A female patient, aged around 70 · a dermoscopic view of a skin lesion — 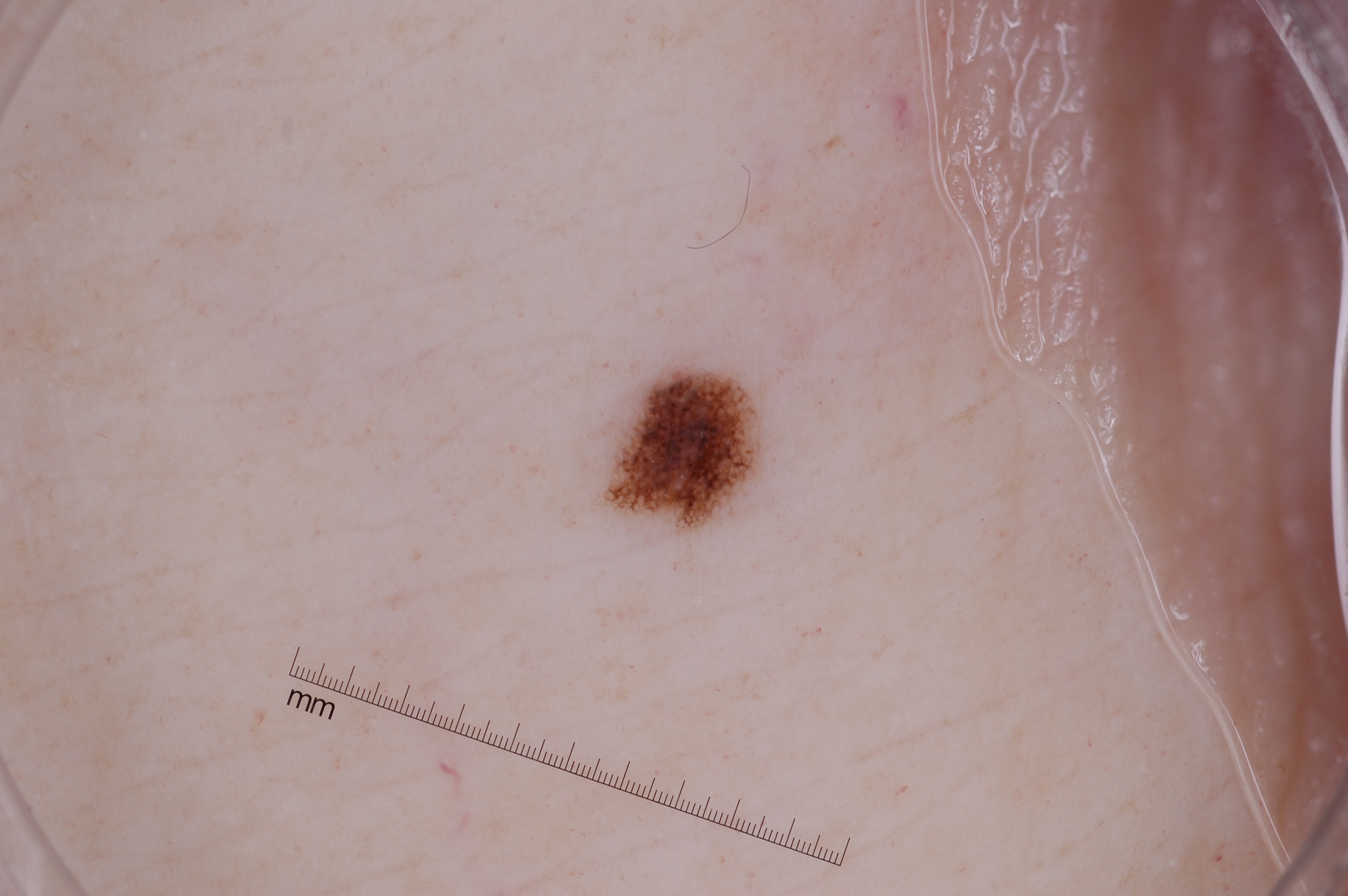Q: Where is the lesion located?
A: <bbox>622, 378, 747, 518</bbox>
Q: What does dermoscopy show?
A: milia-like cysts and pigment network
Q: What is this lesion?
A: a melanocytic nevus, a benign skin lesion